Skin tone: Fitzpatrick phototype II; the lesion is described as raised or bumpy; associated systemic symptoms include mouth sores; a close-up photograph; present for one to three months; male patient, age 50–59; the contributor reports itching; the affected area is the head or neck:
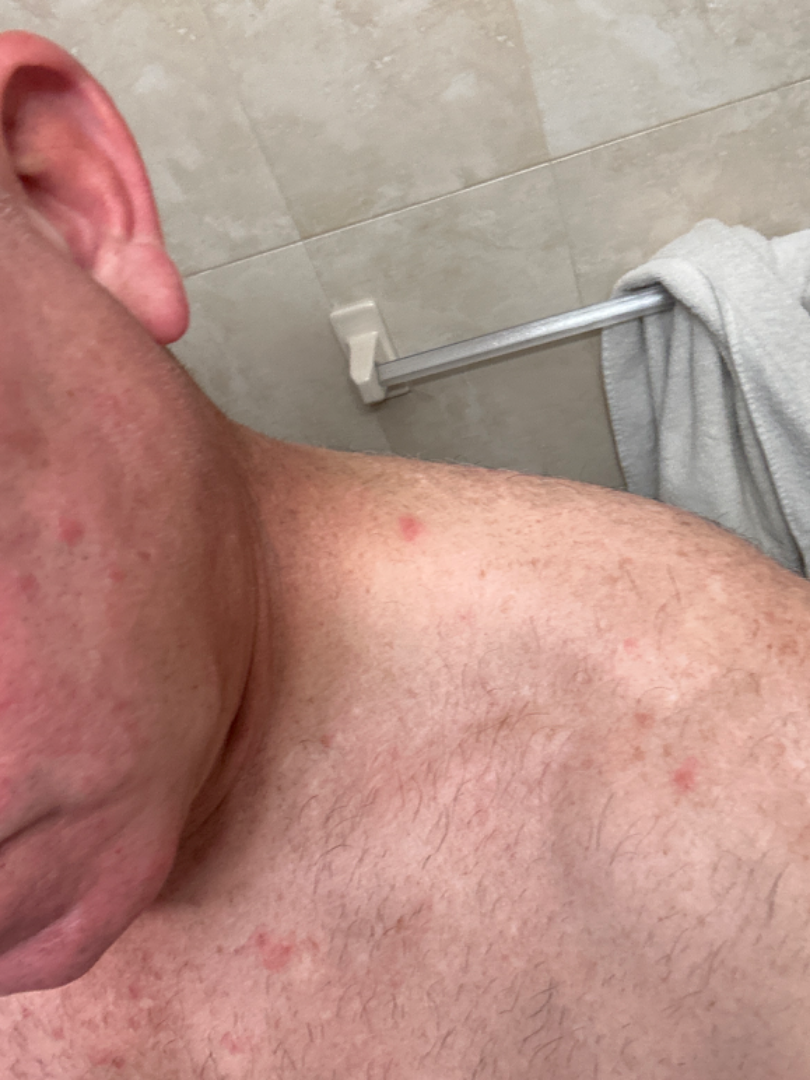The skin findings could not be characterized from the image.